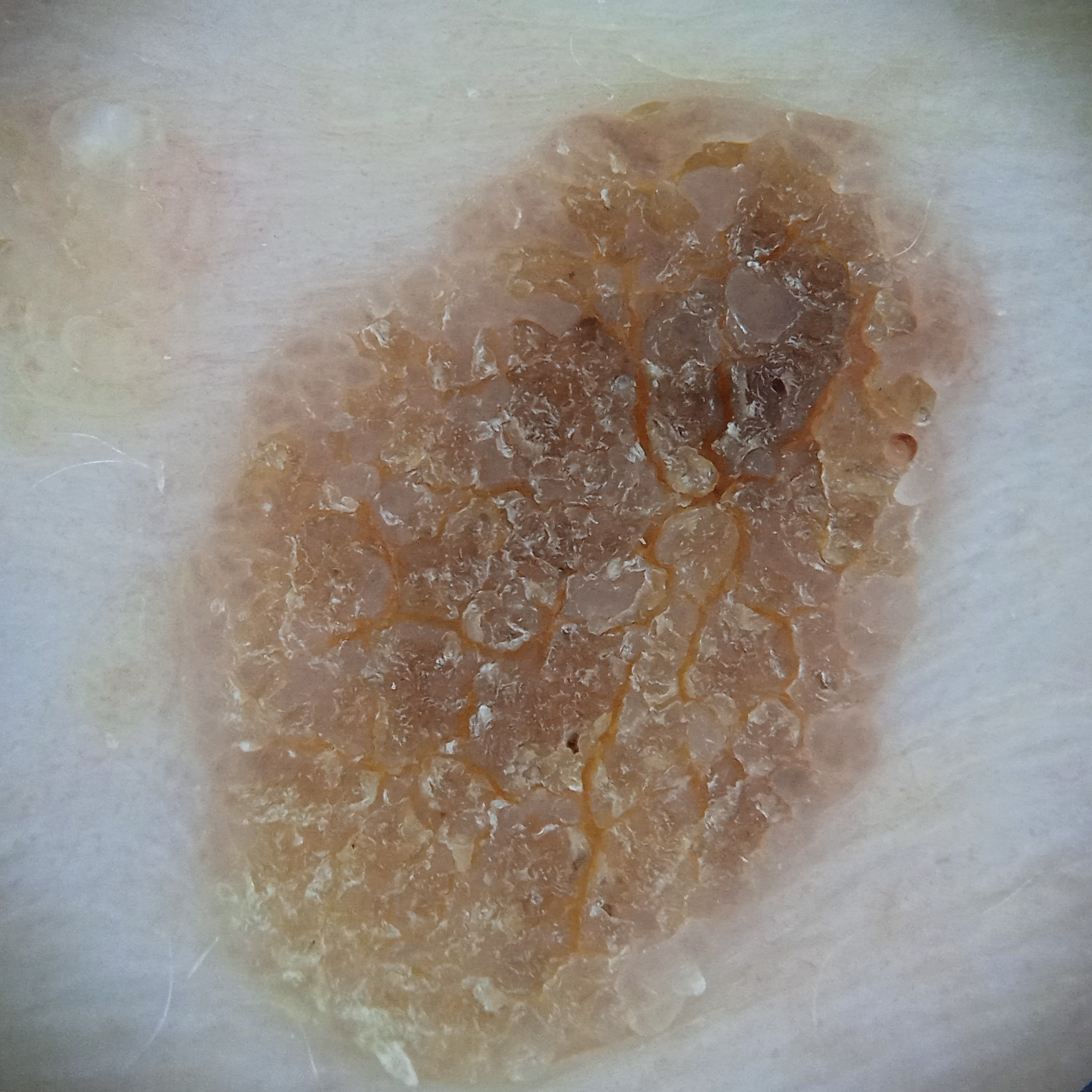Findings: A female patient 81 years old. Dermoscopy of a skin lesion. A moderate number of moles by the patient's own estimate. The patient says their skin reddens painfully with sun exposure. Acquired for a research image collection, with no referral diagnosis. The lesion involves the torso. Measuring roughly 12.2 mm. Impression: The consensus diagnosis for this lesion was a seborrheic keratosis.